Fitzpatrick phototype II · a female subject age 53 · the chart records prior malignancy (patient or family), pesticide exposure, prior skin cancer (patient or family), and no tobacco use · a clinical close-up photograph of a skin lesion.
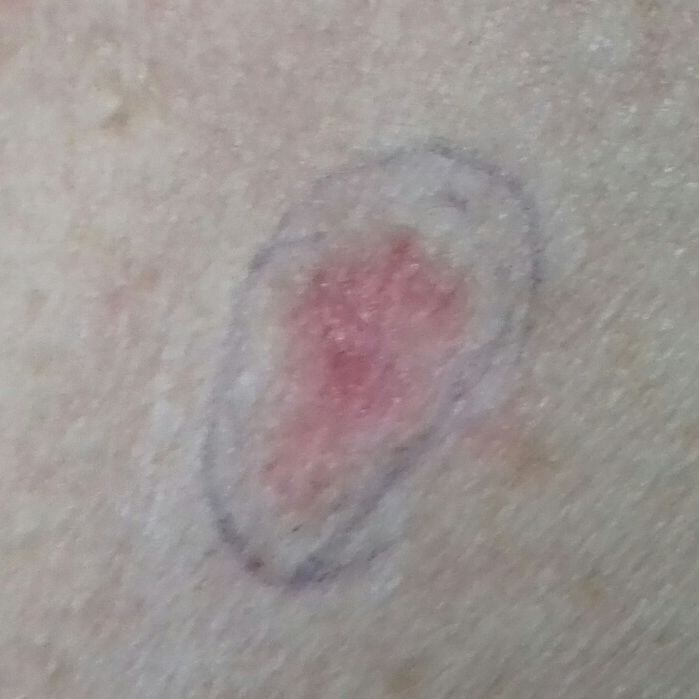• location: the back
• lesion diameter: 16 × 10 mm
• reported symptoms: itching, growth, elevation / no pain
• diagnostic label: basal cell carcinoma (biopsy-proven)